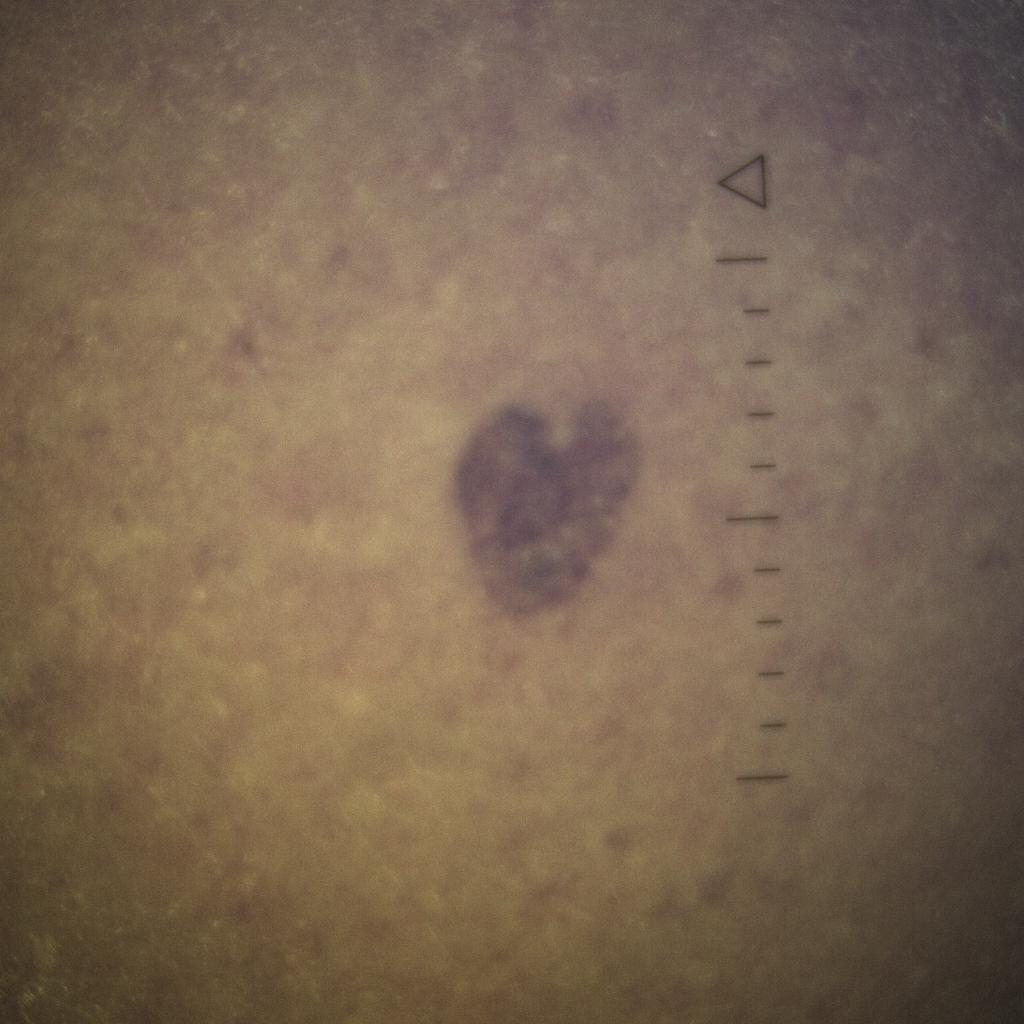nevus count: few melanocytic nevi overall | relevant history: a personal history of skin cancer, no family history of skin cancer | referral: research study (no referral diagnosis) | sun reaction: skin tans without first burning | patient: male, 67 years of age | lesion size: 4.4 mm | diagnostic label: seborrheic keratosis (dermatologist consensus).